An overview clinical photograph of a skin lesion. A male subject aged 68 to 72.
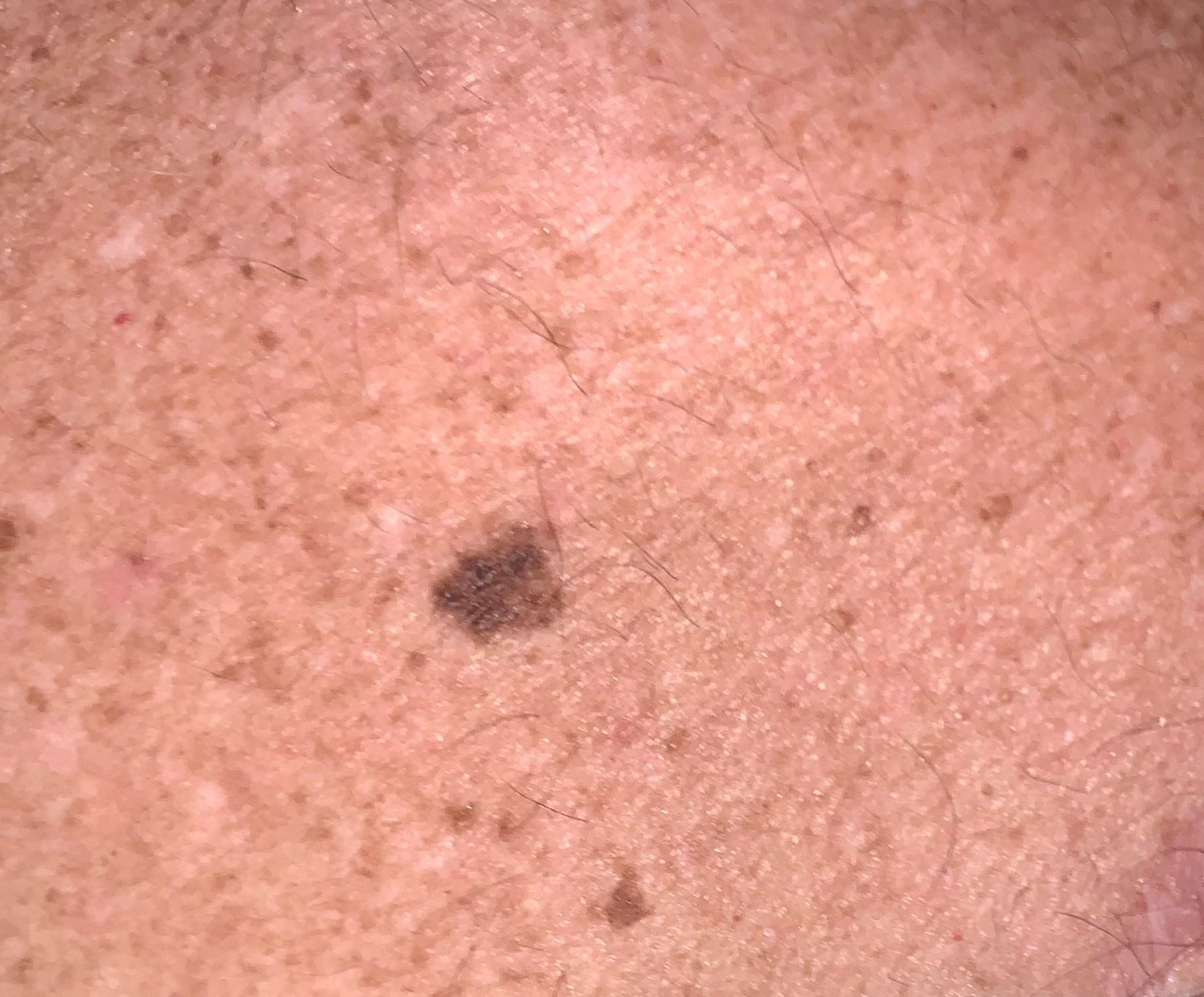Case summary: The lesion involves the trunk. Diagnosis: Confirmed on histopathology as a nevus.